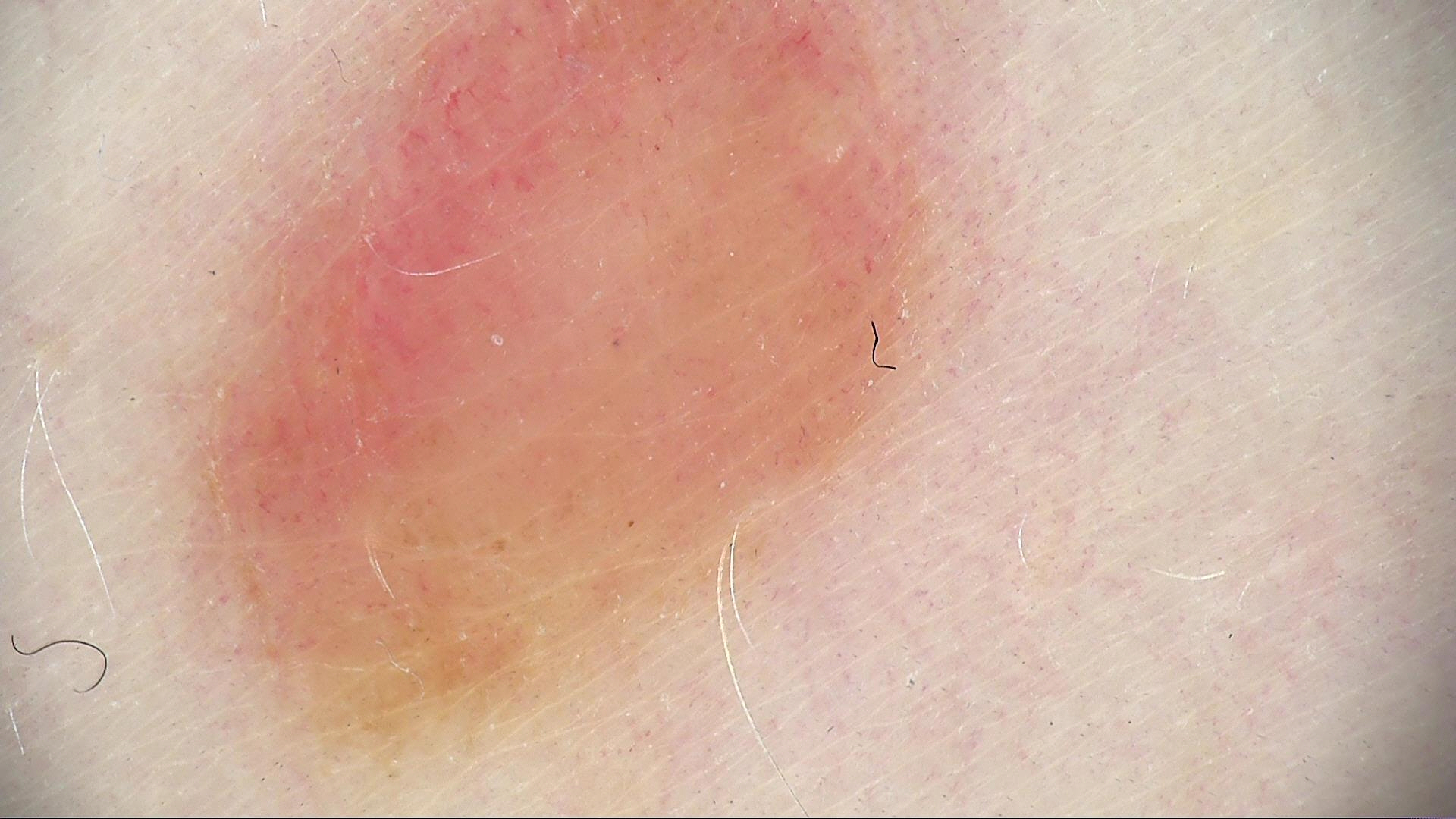| key | value |
|---|---|
| image | dermoscopy |
| classification | banal |
| label | junctional nevus (expert consensus) |